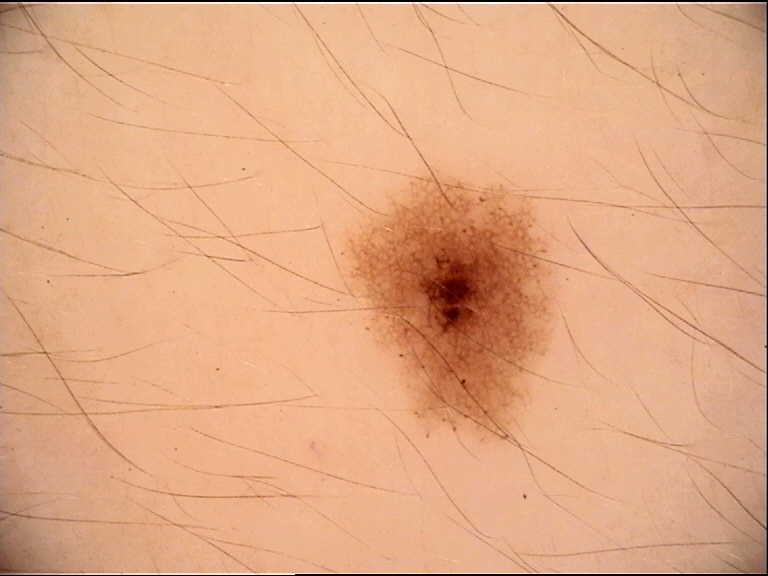Classified as a dysplastic junctional nevus.